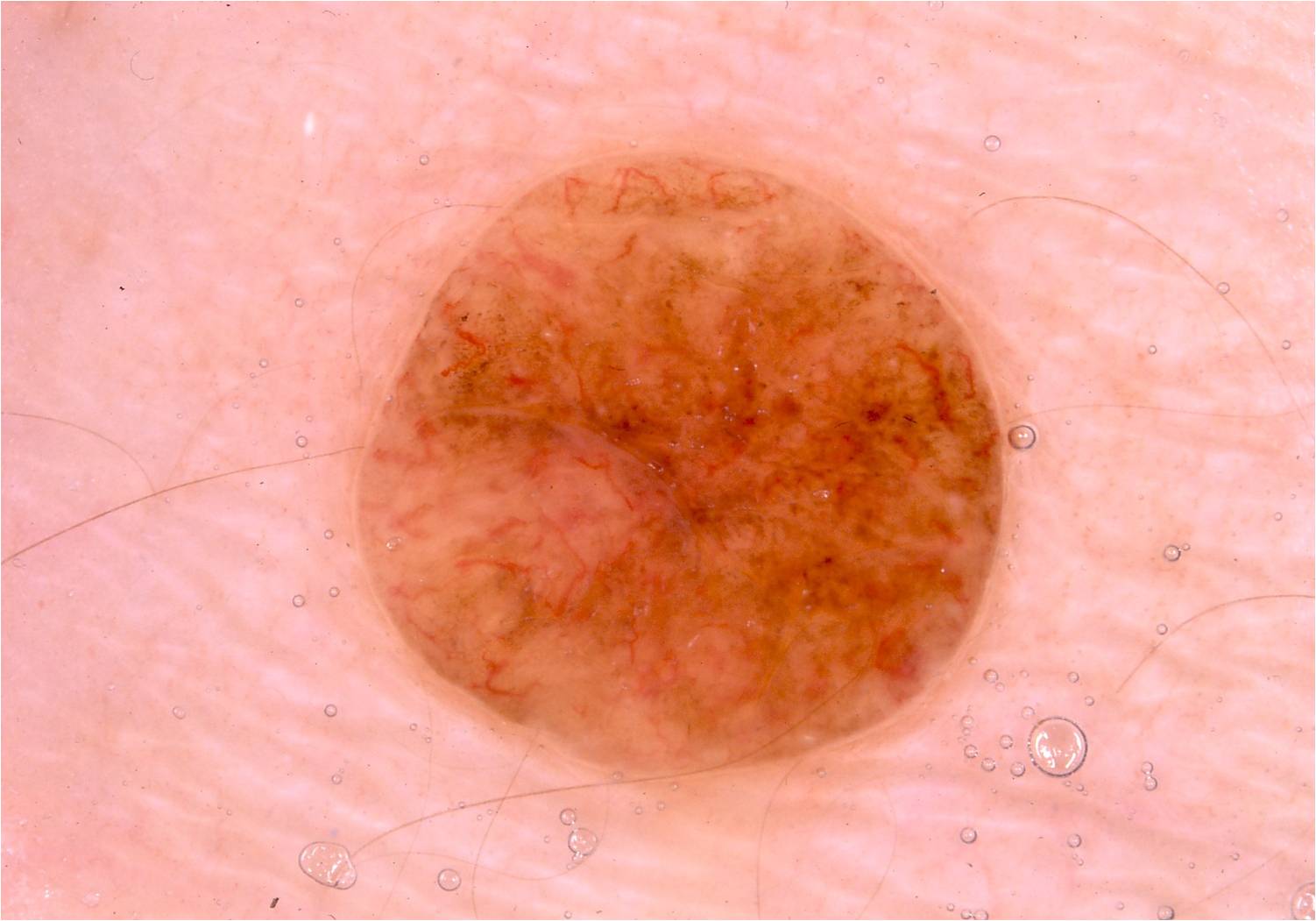patient = male, in their mid- to late 40s
modality = dermoscopy
dermoscopic pattern = pigment network
lesion extent = ~27% of the field
location = 348/149/1010/783
diagnosis = a melanocytic nevus